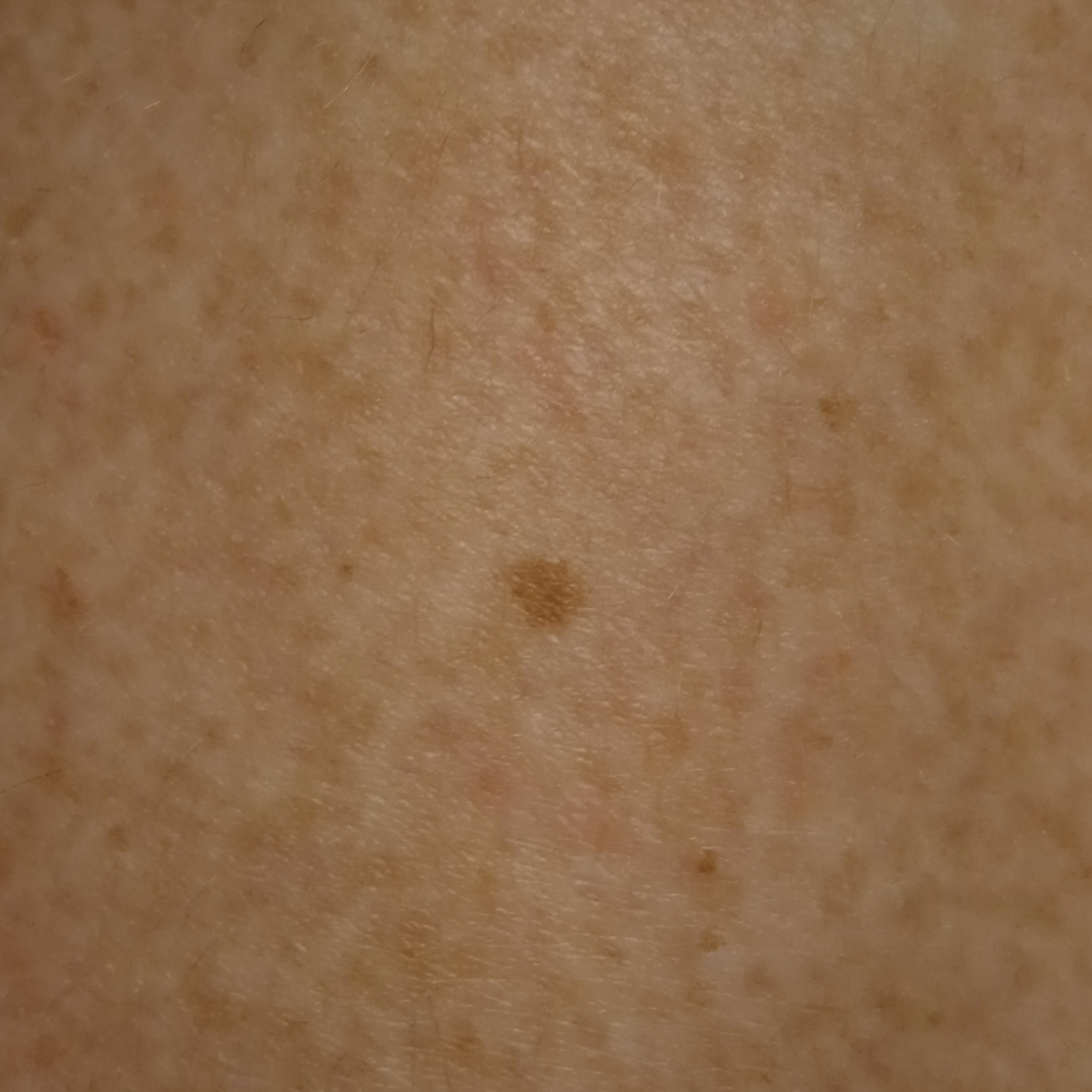referral context: research study (no referral diagnosis); nevus count: a moderate number of melanocytic nevi; patient: female, age 53; sun reaction: skin reddens with sun exposure; site: a leg; diagnosis: melanocytic nevus (dermatologist consensus).